This is a dermoscopic photograph of a skin lesion, the subject is a male in their mid- to late 50s.
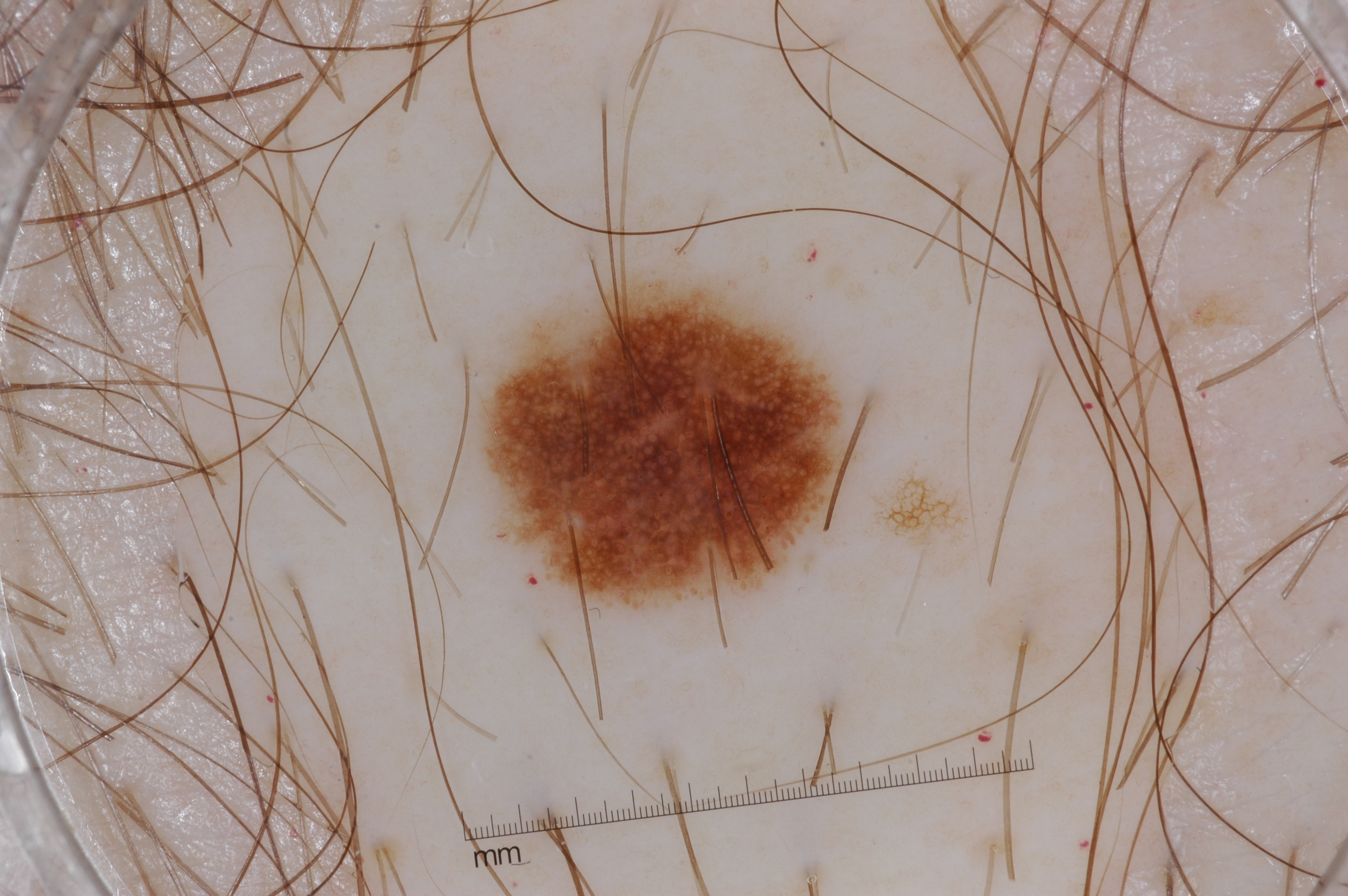Summary:
Dermoscopy demonstrates pigment network; no negative network, milia-like cysts, or streaks. In (x1, y1, x2, y2) order, the lesion is bounded by 485, 287, 842, 602.
Impression:
Diagnosed as a melanocytic nevus, a benign lesion.